A skin lesion imaged with a dermatoscope:
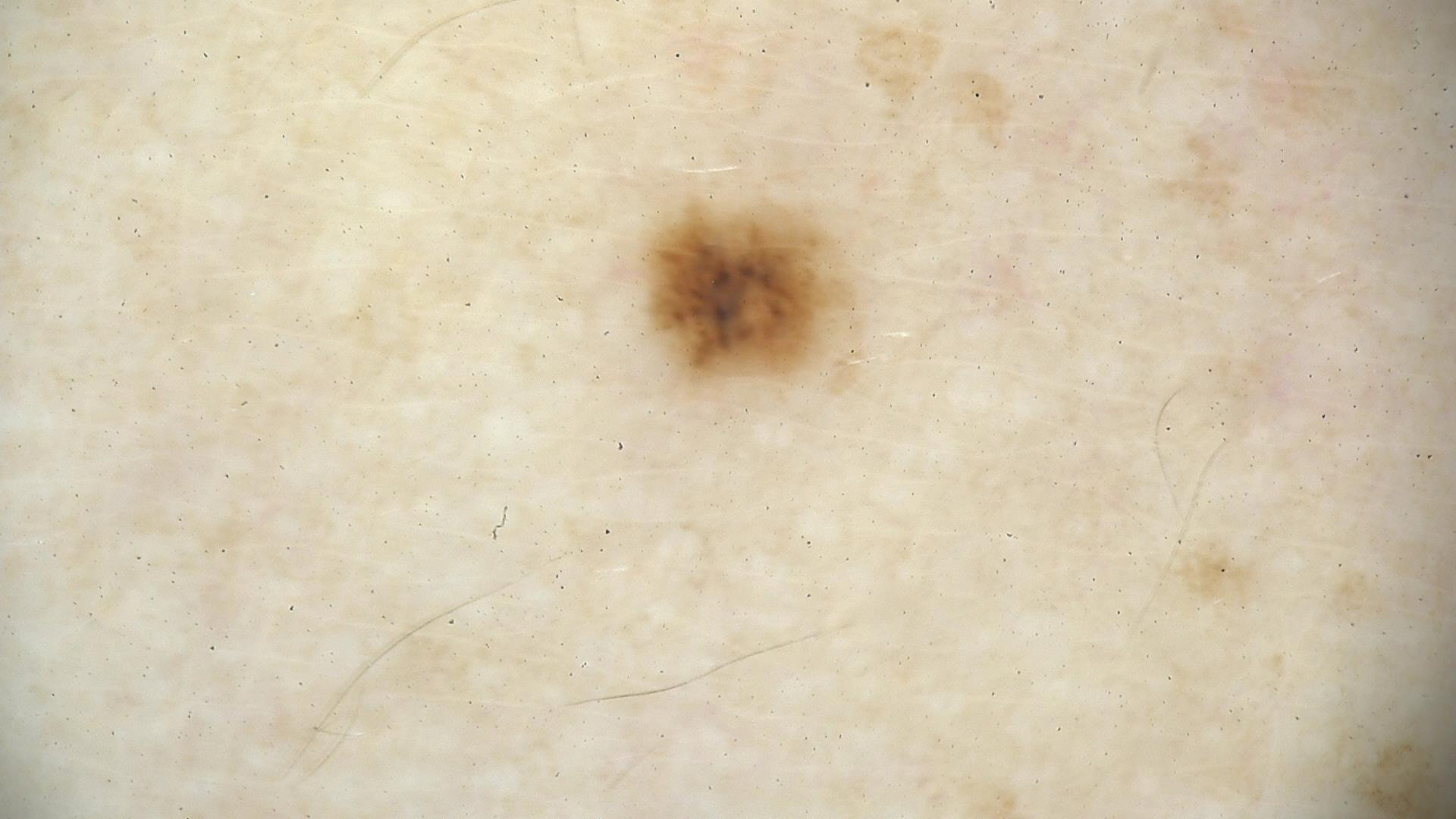The diagnostic label was a benign lesion — a dysplastic junctional nevus.